The contributor reports the lesion is fluid-filled and raised or bumpy; the condition has been present for less than one week; this is a close-up image; reported lesion symptoms include itching and burning; male patient, age 18–29; the patient reported no systemic symptoms; the affected area is the leg; the patient described the issue as a rash — 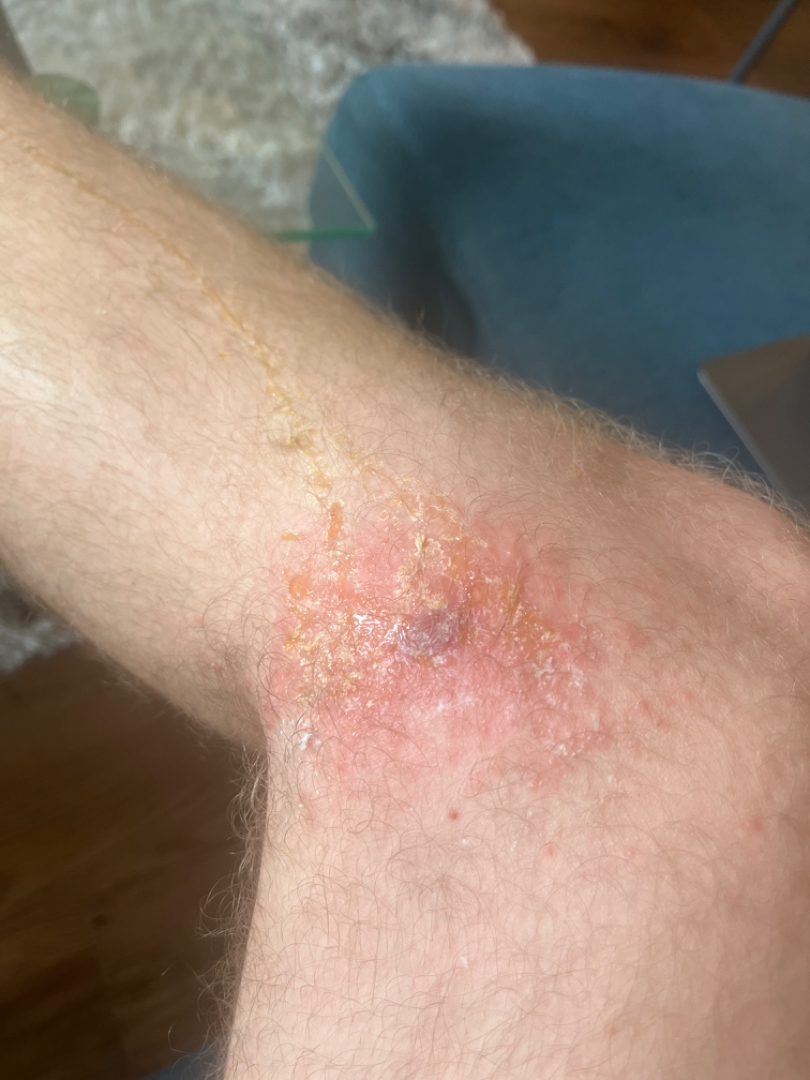Assessment: The reviewing dermatologist's impression was: most consistent with Insect Bite.